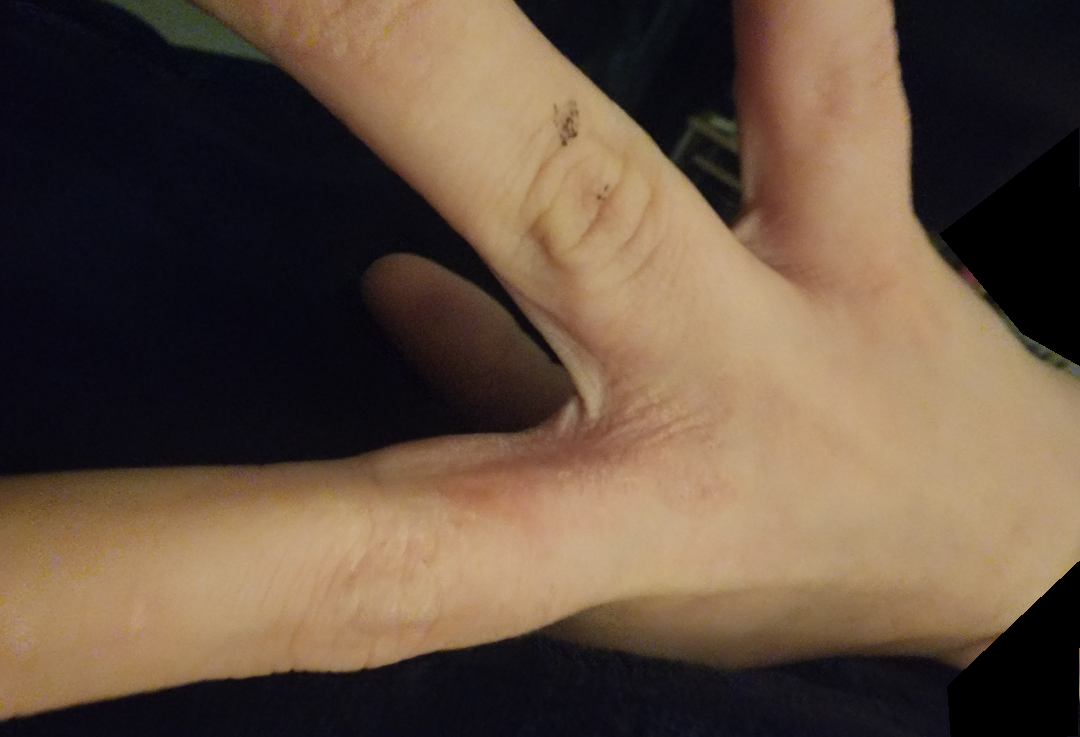On remote review of the image: the favored diagnosis is Eczema; also consider Tinea; with consideration of Psoriasis.